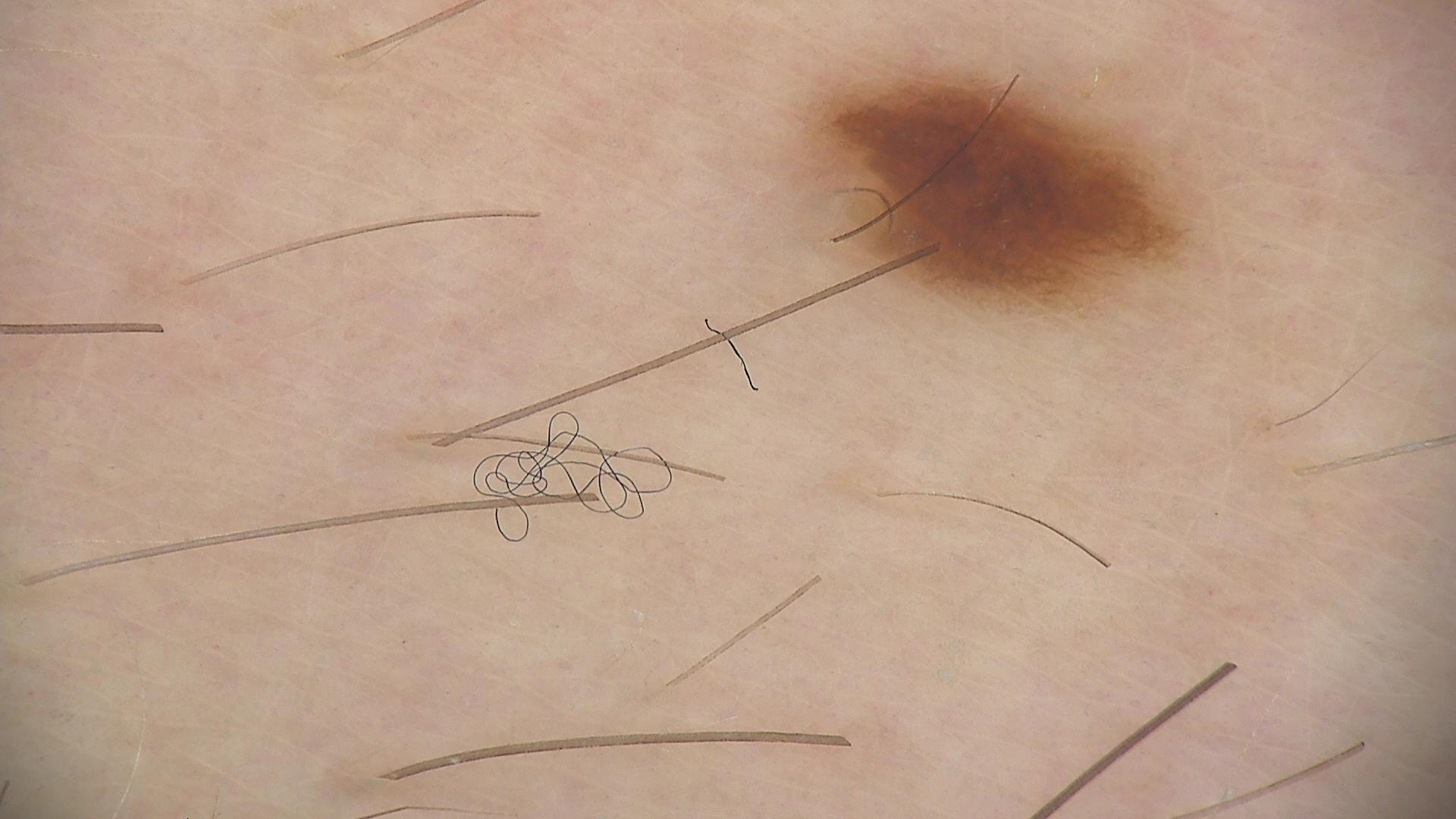Impression: Labeled as a junctional nevus.